The patient described the issue as a rash; the patient notes the lesion is rough or flaky; close-up view; symptoms reported: burning, enlargement, pain, bothersome appearance and itching; the patient notes the condition has been present for one to four weeks; the patient reported no systemic symptoms:
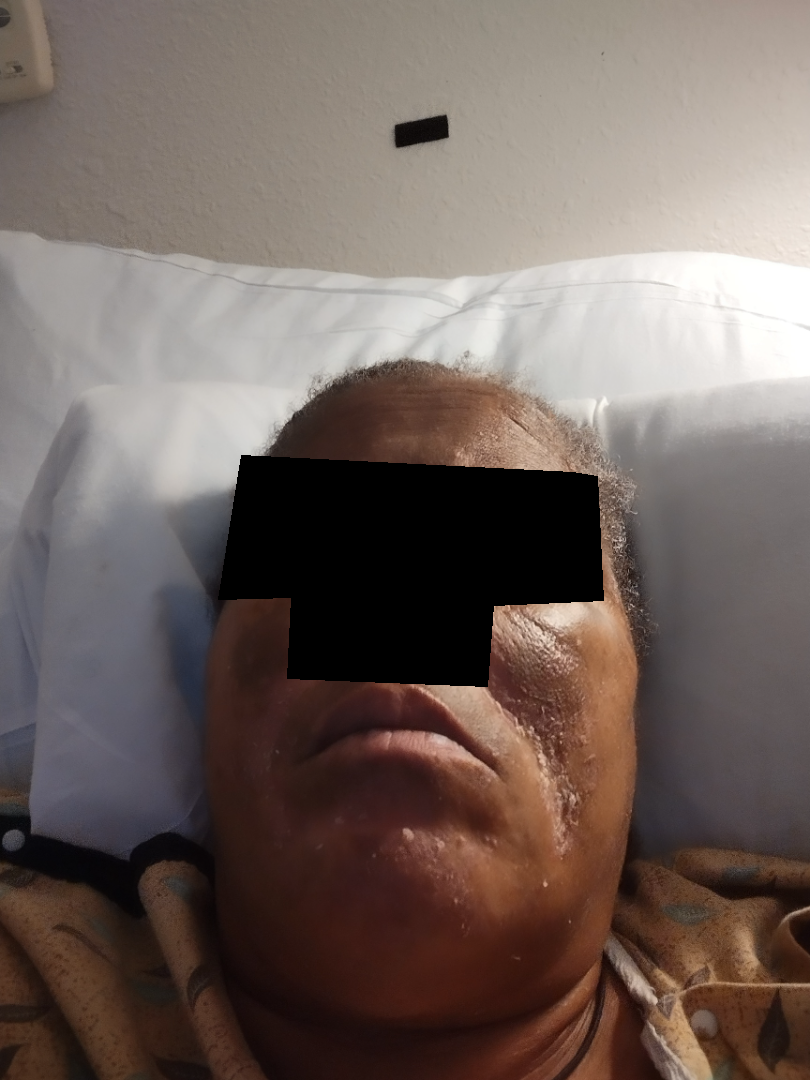Diagnostic features were not clearly distinguishable in this photograph.